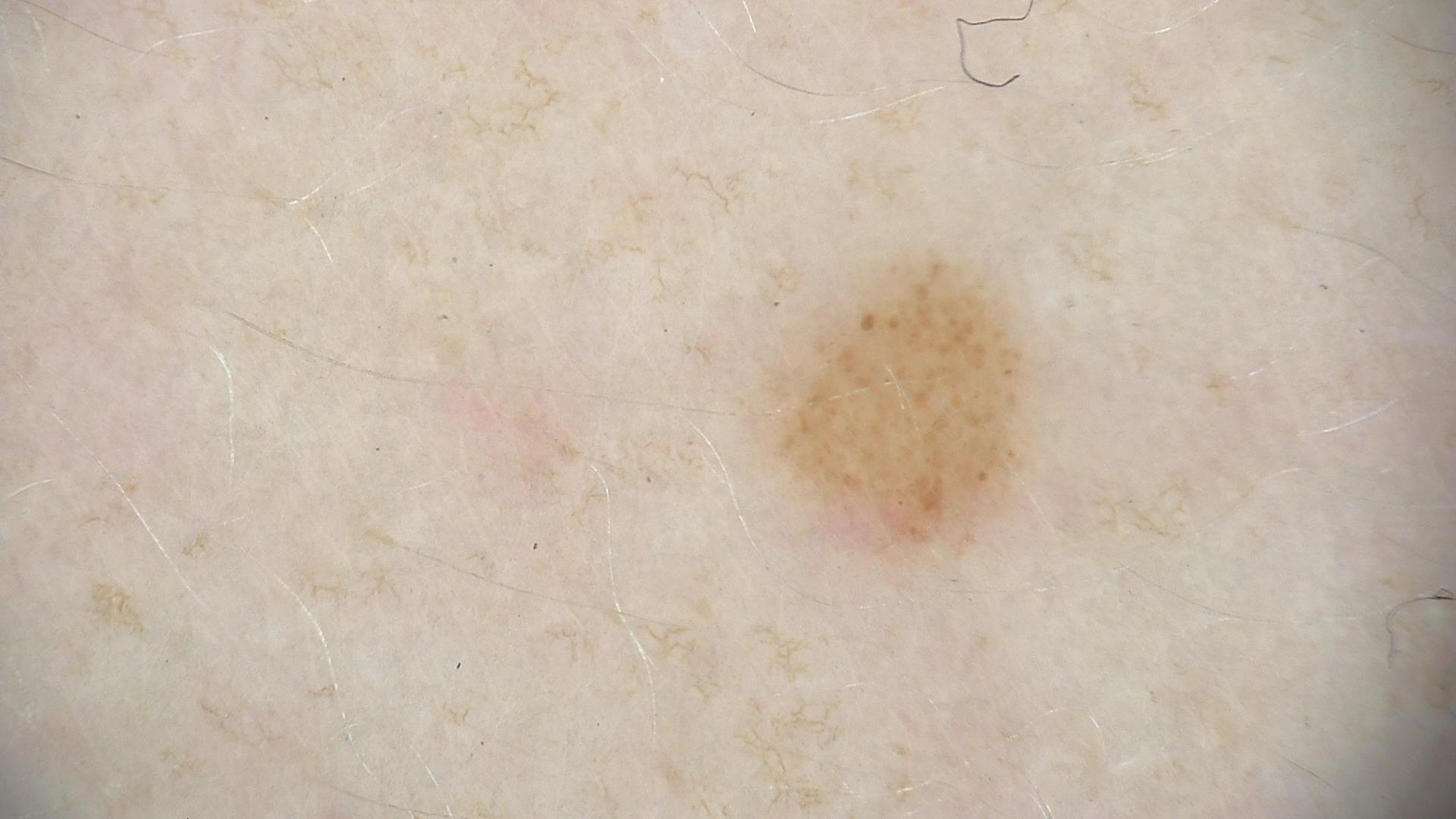Q: What is the imaging modality?
A: dermatoscopy
Q: What is this lesion?
A: dysplastic junctional nevus (expert consensus)